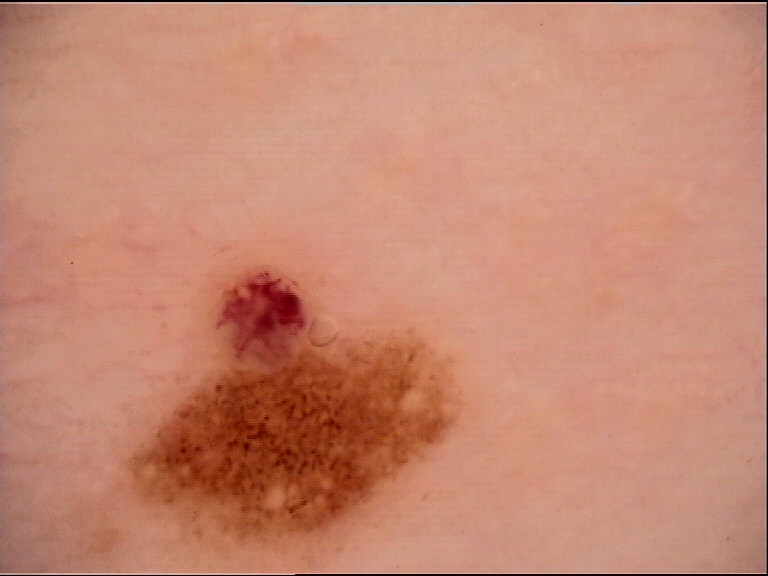Case:
* image type · dermoscopy
* assessment · dysplastic junctional nevus (expert consensus)